The photograph is a close-up of the affected area, self-categorized by the patient as a rash, the patient reports itching, the condition has been present for one to four weeks, texture is reported as rough or flaky, no relevant systemic symptoms, the lesion involves the arm:
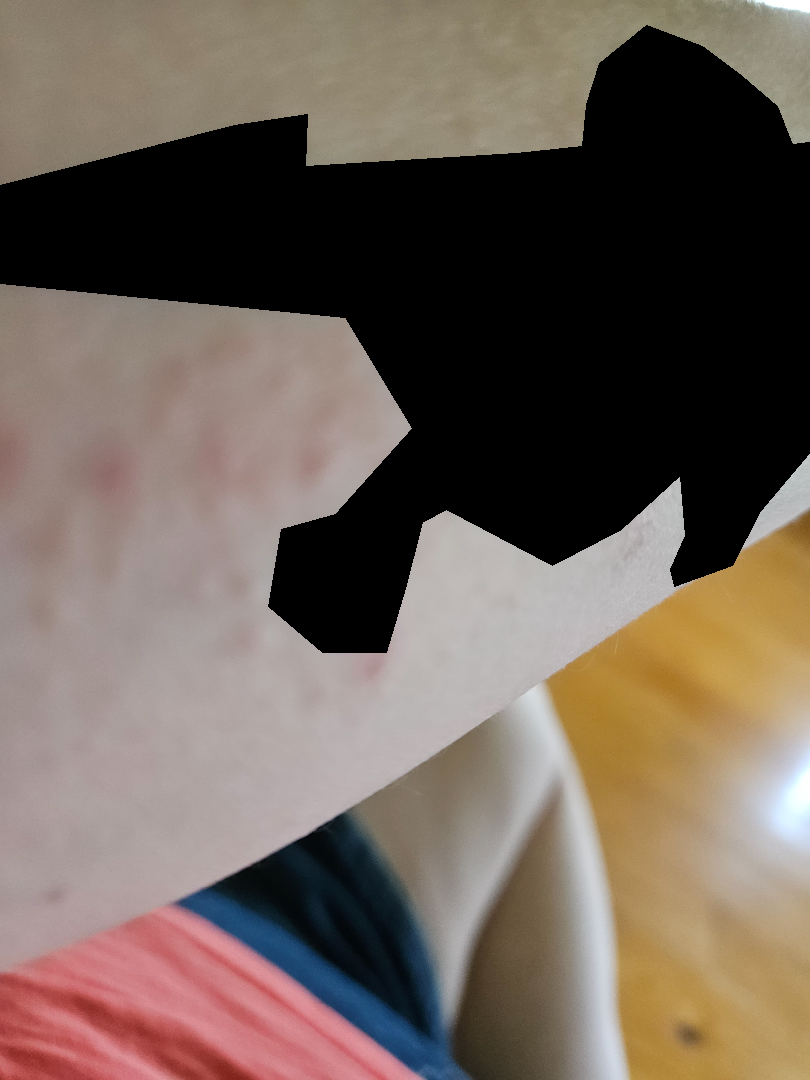The case was difficult to assess from the available photograph.